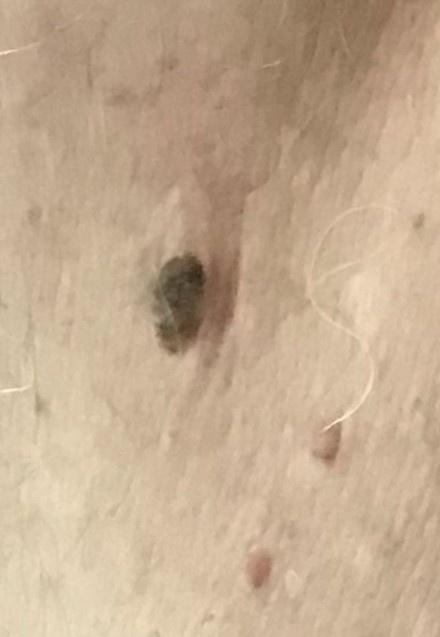• subject — male, roughly 70 years of age
• risk factors — a first-degree relative with melanoma
• imaging — clinical overview photograph
• diagnosis — Nevus (clinical impression)